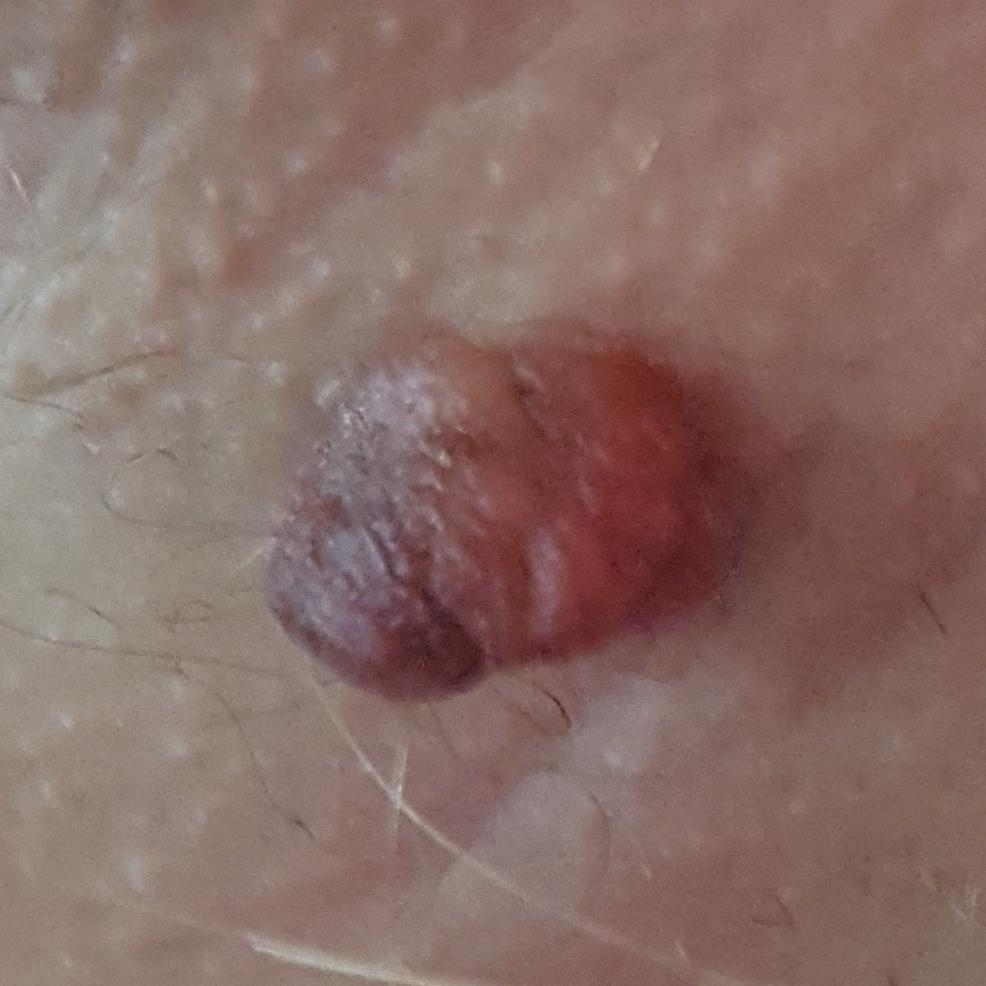{
  "image": "clinical photo",
  "patient": {
    "age": 25
  },
  "lesion_location": "an arm",
  "symptoms": {
    "present": [
      "elevation",
      "growth"
    ],
    "absent": [
      "change in appearance"
    ]
  },
  "diagnosis": {
    "name": "nevus",
    "code": "NEV",
    "malignancy": "benign",
    "confirmation": "clinical consensus"
  }
}